The photograph was taken at an angle · the leg is involved · the subject is a male aged 18–29: 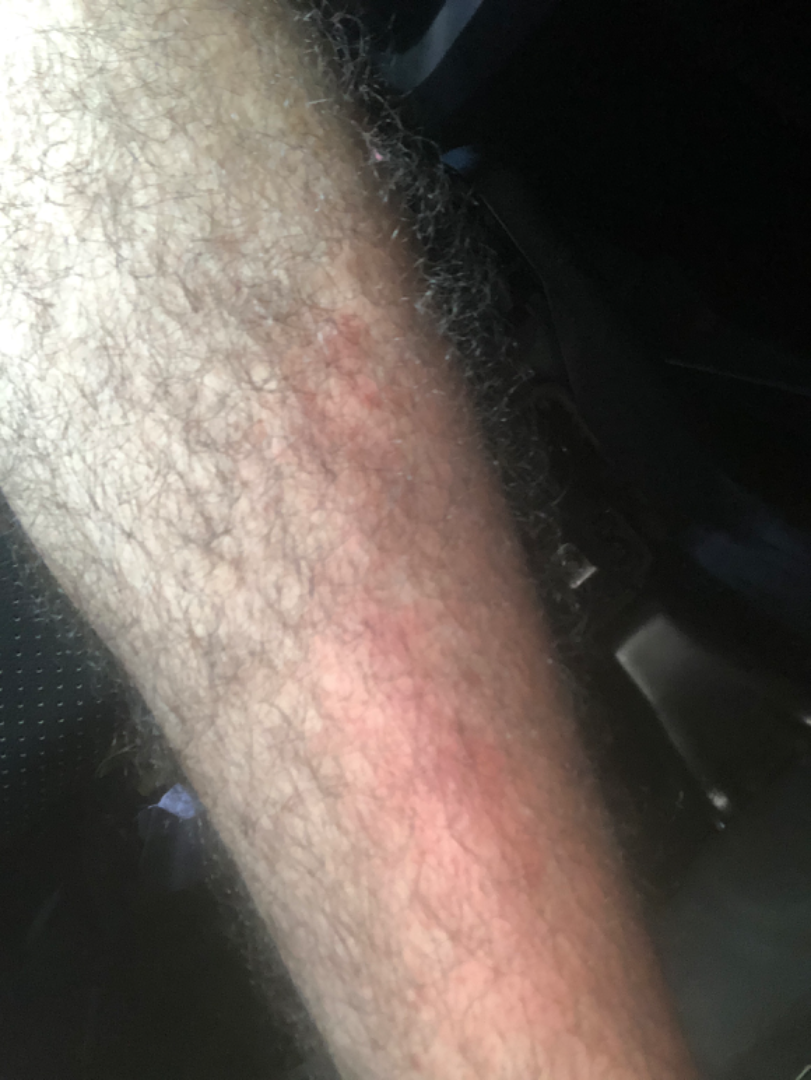Impression:
On teledermatology review, Impetigo (considered); Cellulitis (considered); Eczema (considered).